A dermoscopic view of a skin lesion: 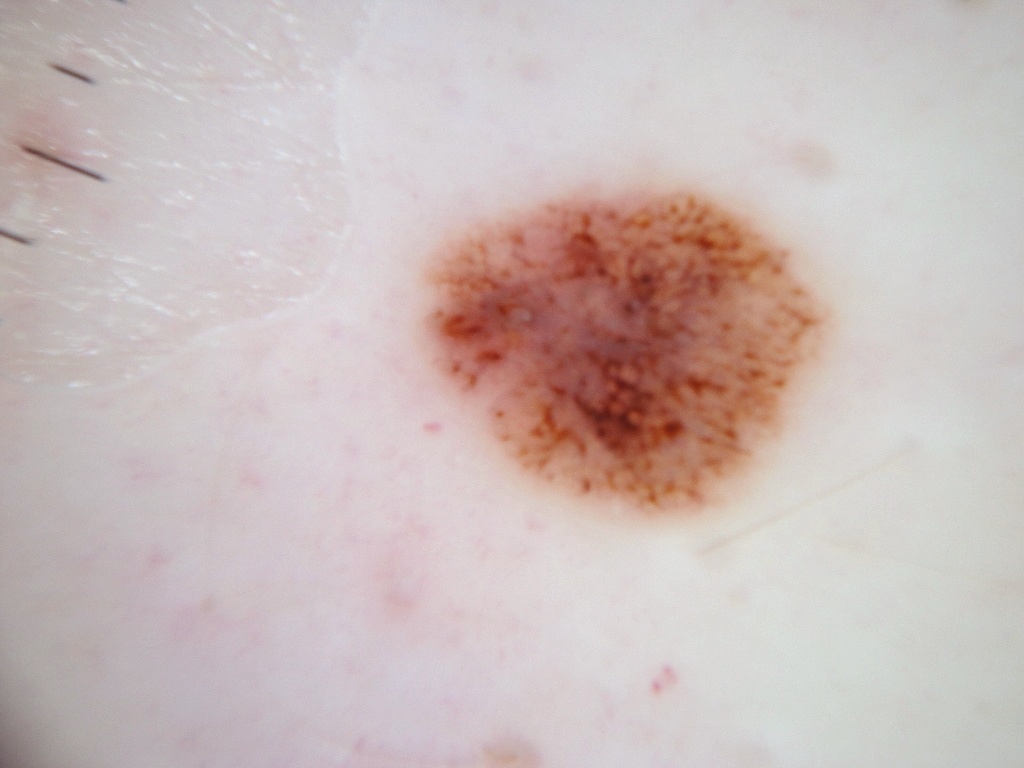bounding box = <box>416, 181, 831, 517</box>; dermoscopic features not present = globules and streaks; diagnosis = a benign skin lesion.